A skin lesion imaged with a dermatoscope:
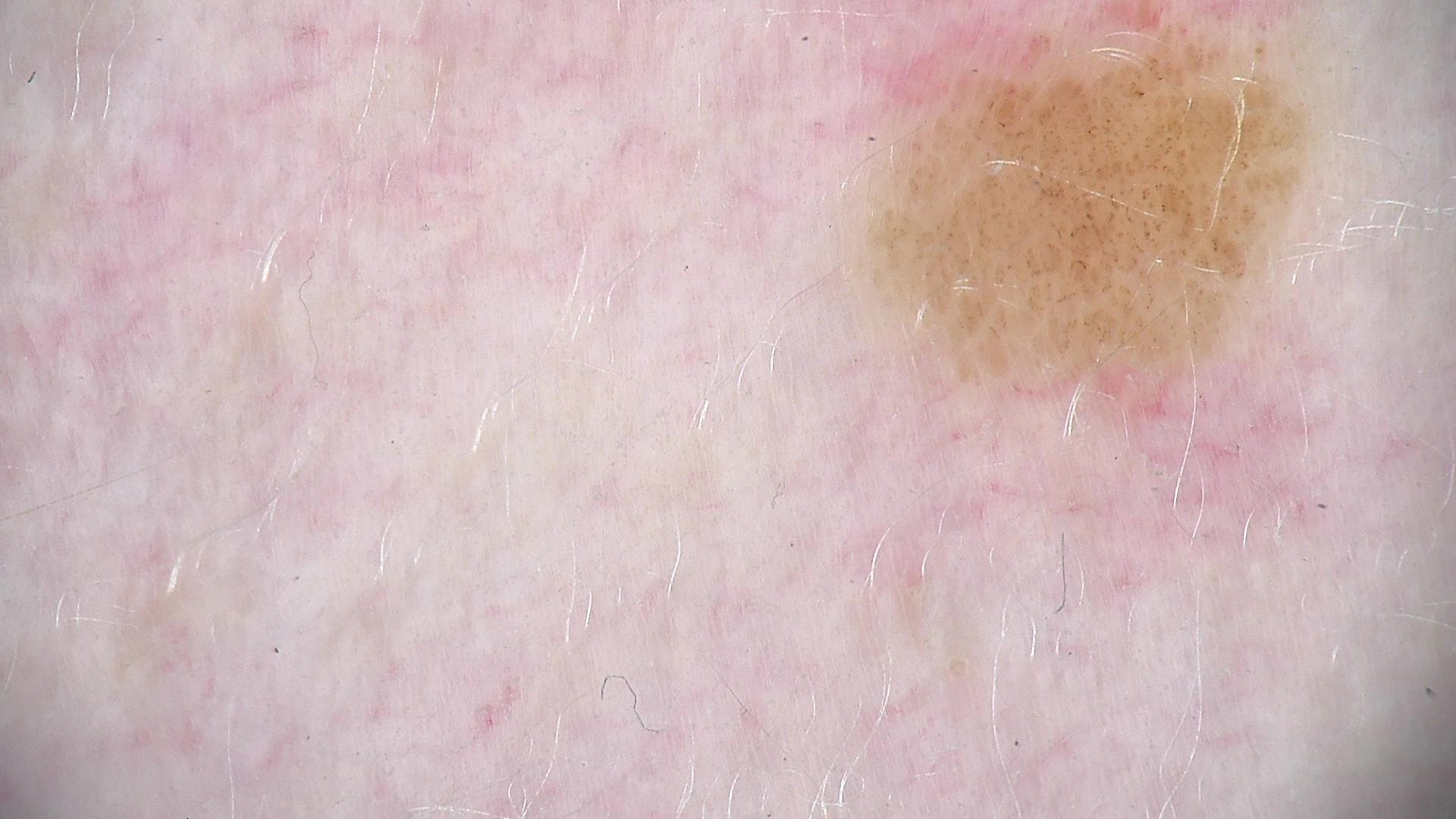category = banal; label = compound nevus (expert consensus).